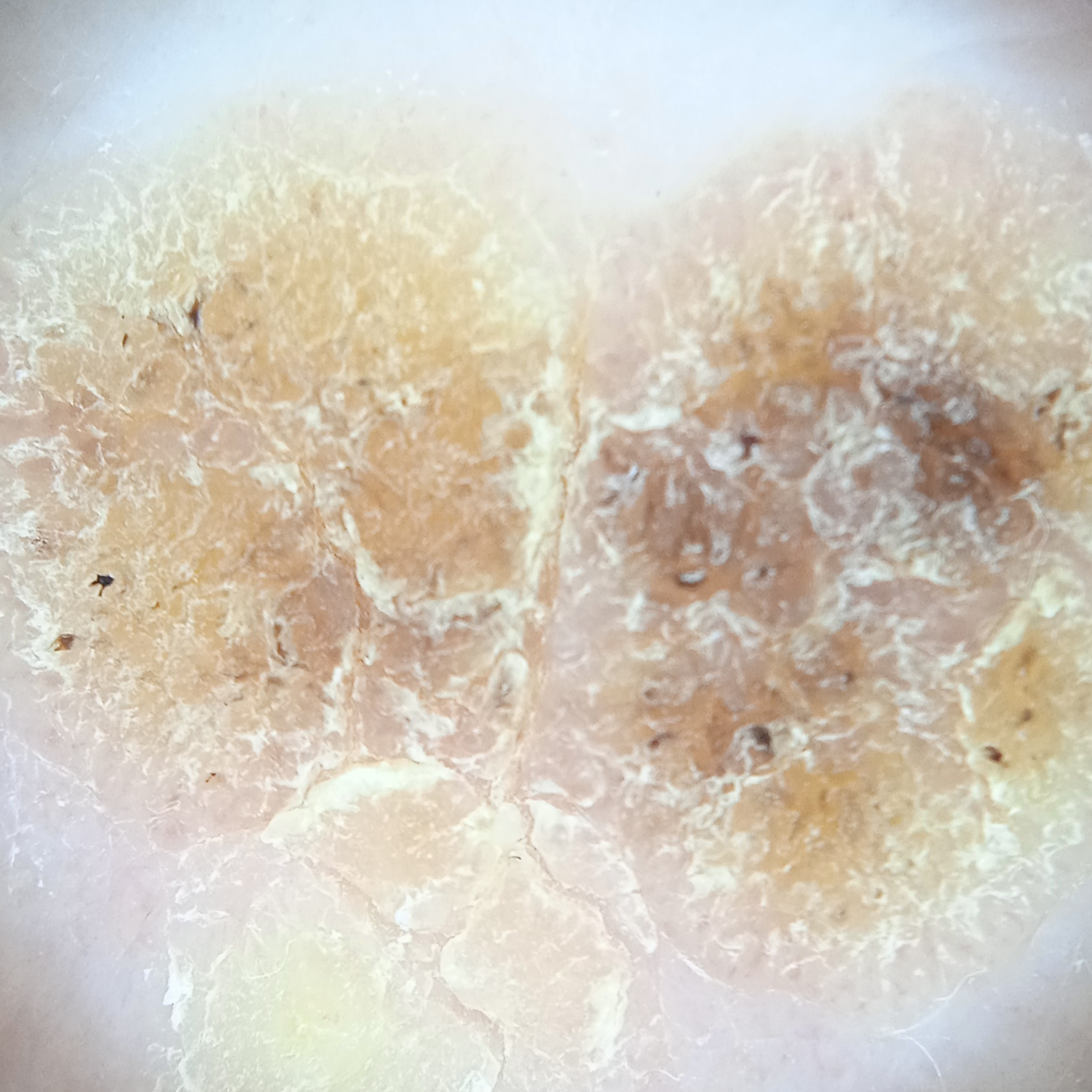relevant history = a personal history of cancer, a personal history of skin cancer | sun reaction = skin reddens with sun exposure | referral context = research study (no referral diagnosis) | nevus count = a moderate number of melanocytic nevi | subject = male, aged 77 | image = dermoscopy | location = the back | lesion size = 14.2 mm | assessment = seborrheic keratosis (dermatologist consensus).